FST IV; lay reviewers estimated MST 3–4, this image was taken at a distance:
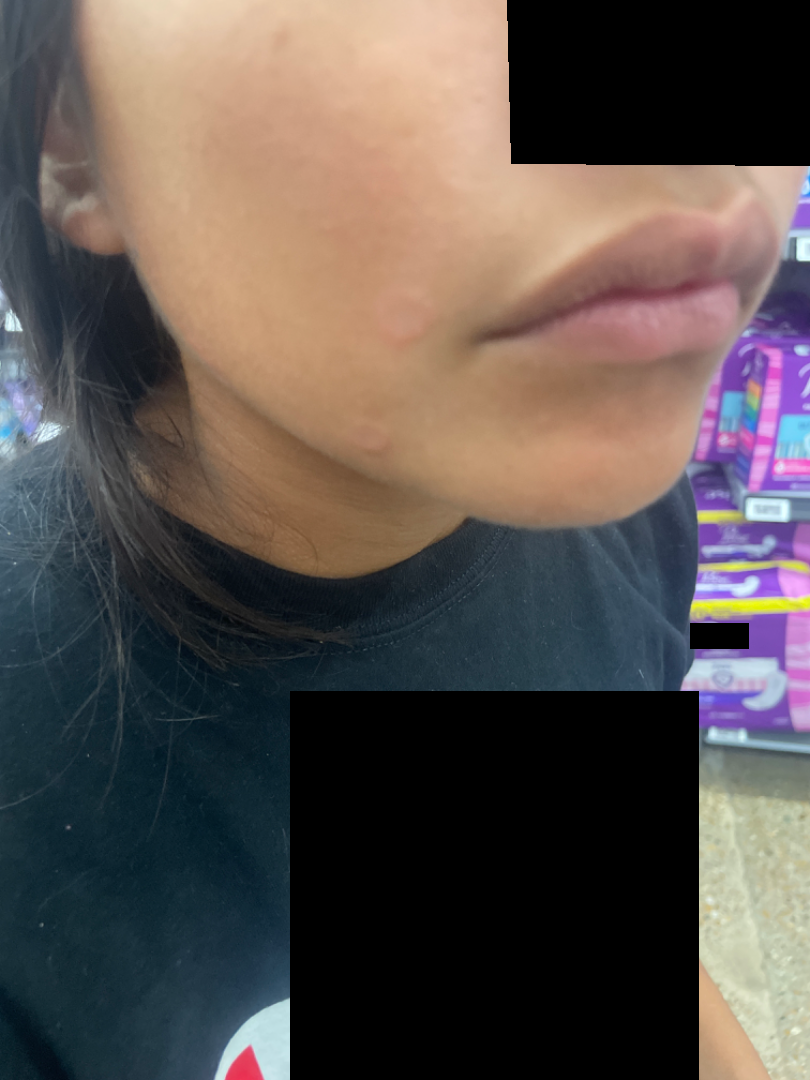assessment = unable to determine